Dermoscopy of a skin lesion.
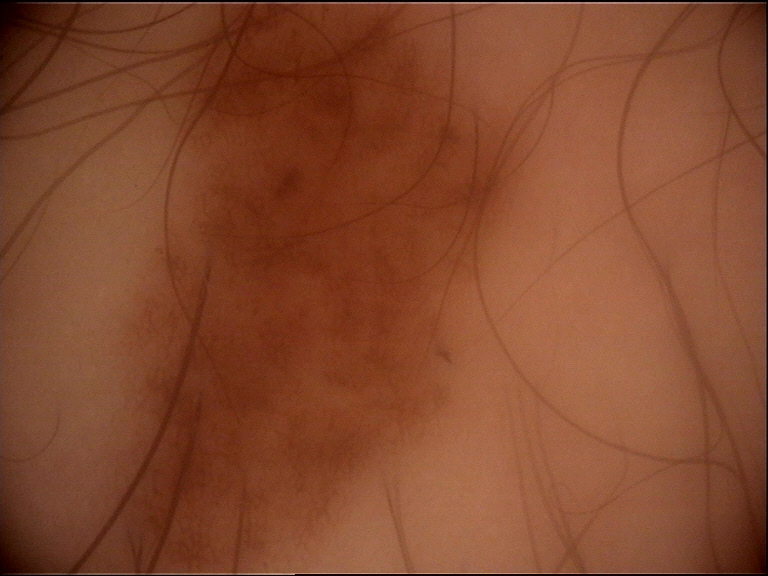Conclusion:
Classified as a dysplastic junctional nevus.